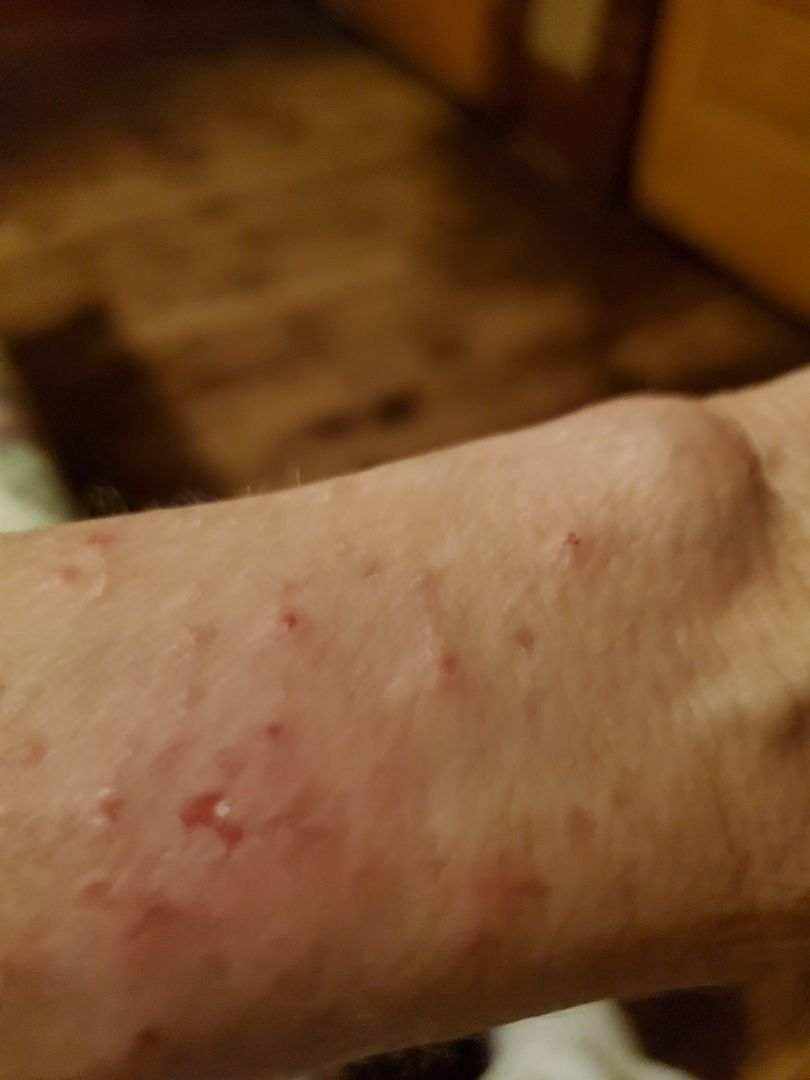The reviewer was unable to grade this case for skin condition.